This is a dermoscopic photograph of a skin lesion — 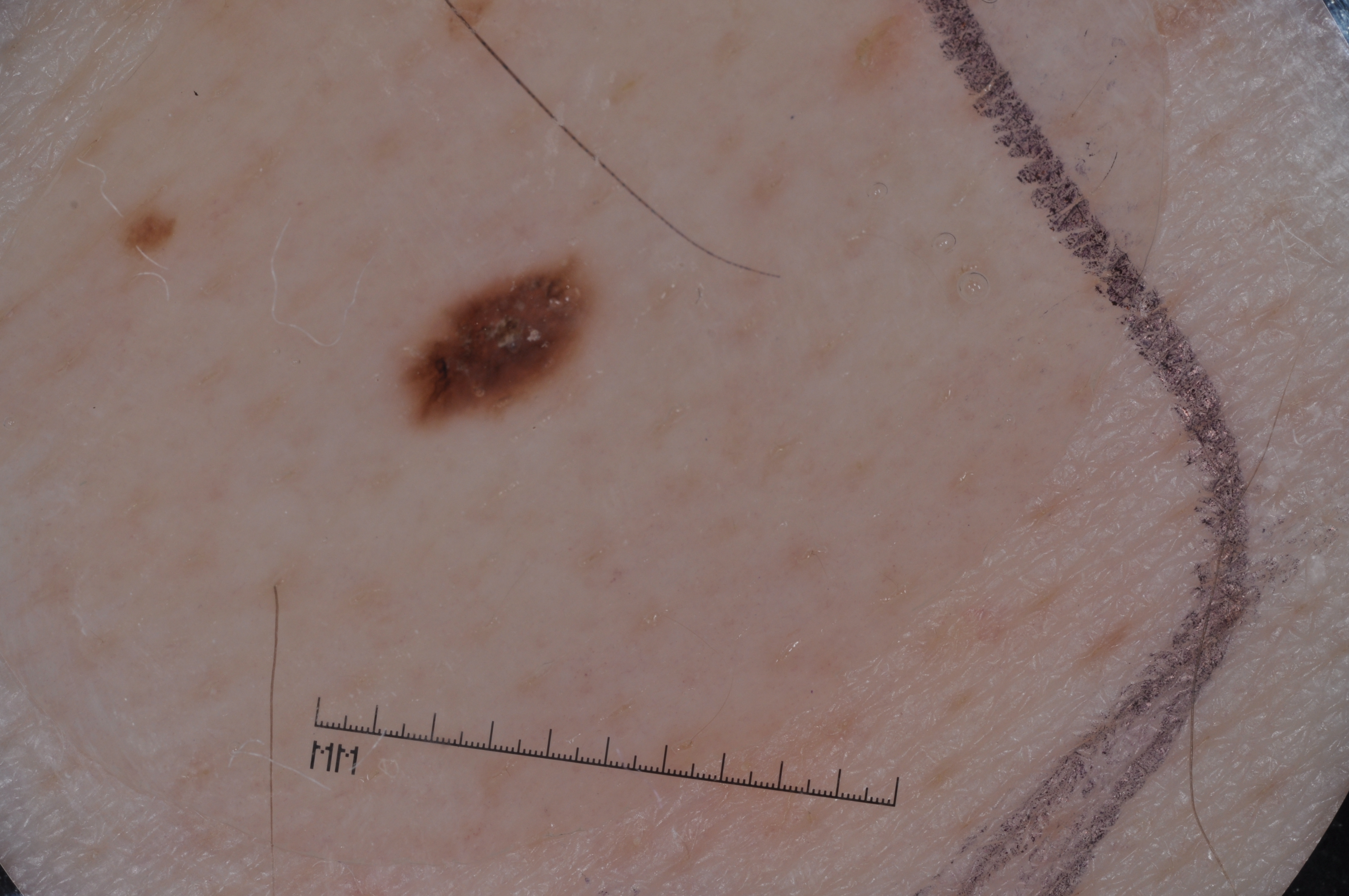<case>
  <lesion_location>
    <bbox_xyxy>397, 255, 597, 428</bbox_xyxy>
  </lesion_location>
  <diagnosis>
    <name>melanoma</name>
    <malignancy>malignant</malignancy>
    <lineage>melanocytic</lineage>
    <provenance>histopathology</provenance>
  </diagnosis>
</case>